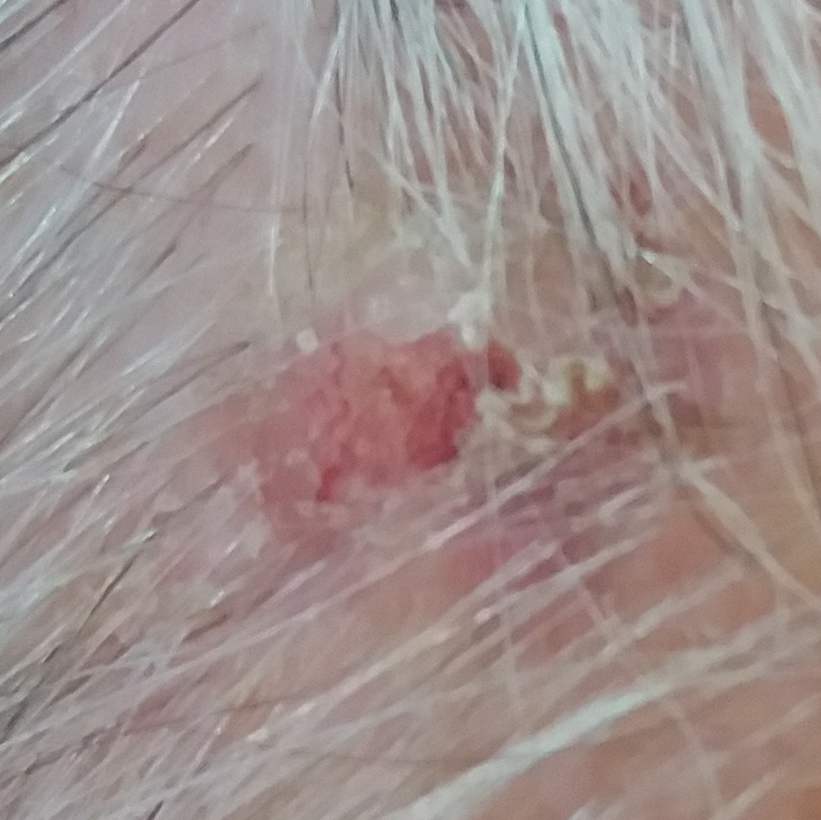Biopsy-confirmed as a basal cell carcinoma.